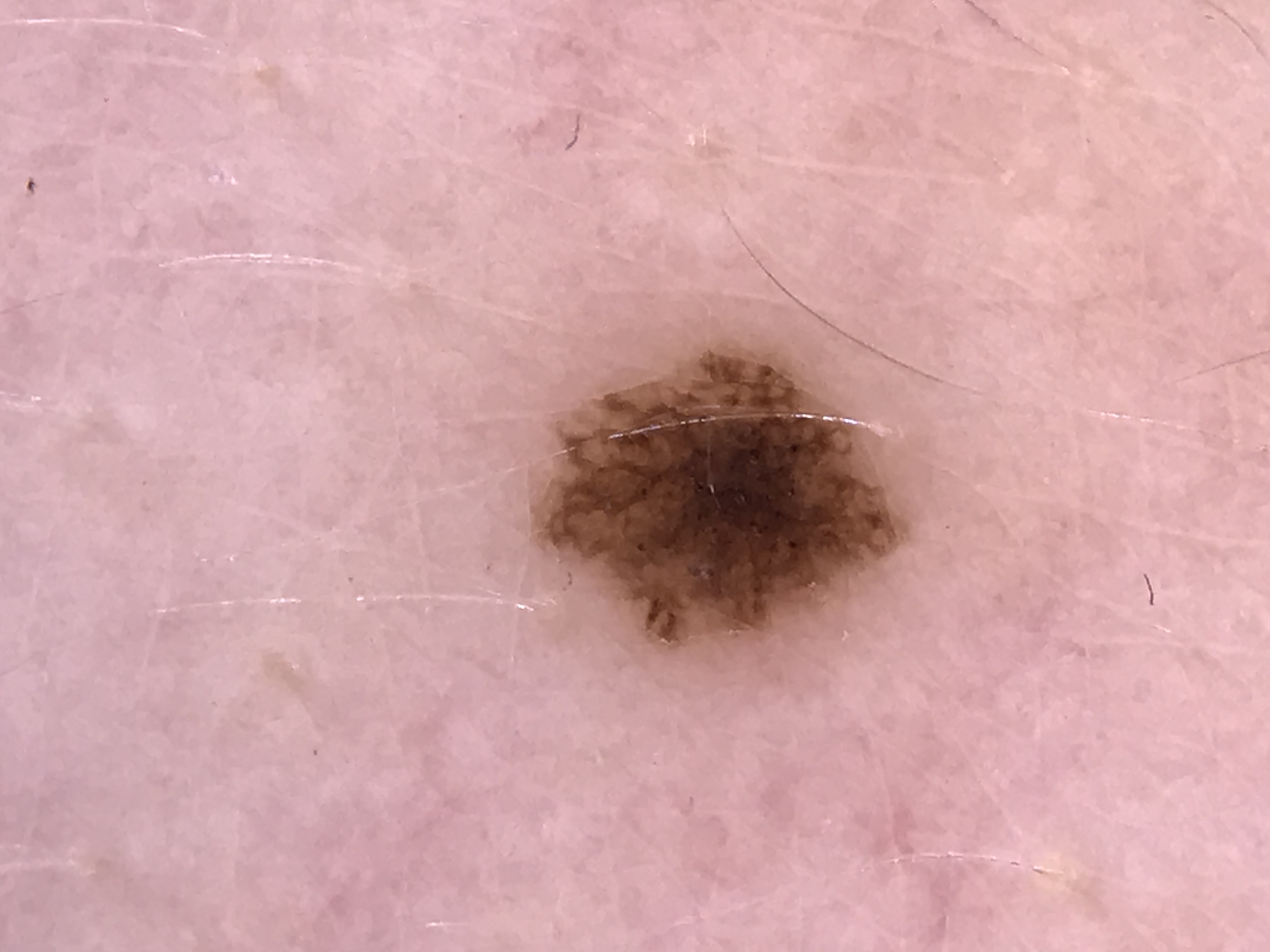diagnosis: dysplastic junctional nevus (expert consensus).